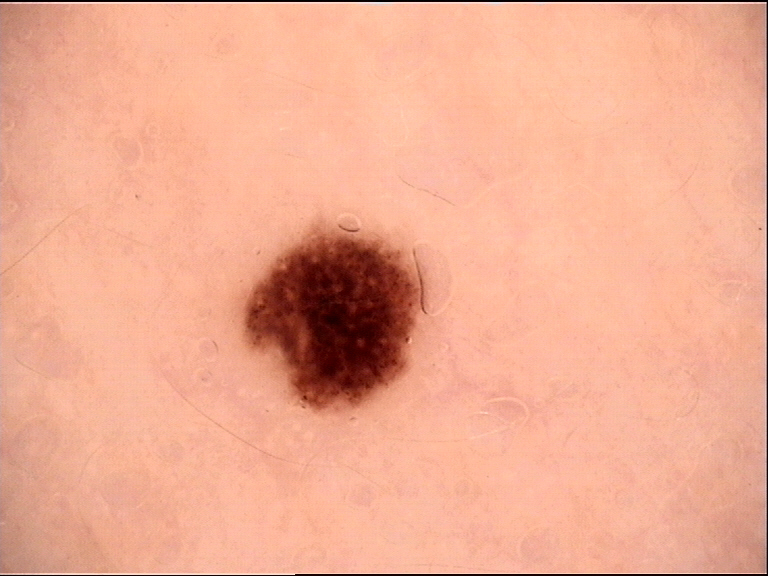Diagnosed as a junctional nevus.